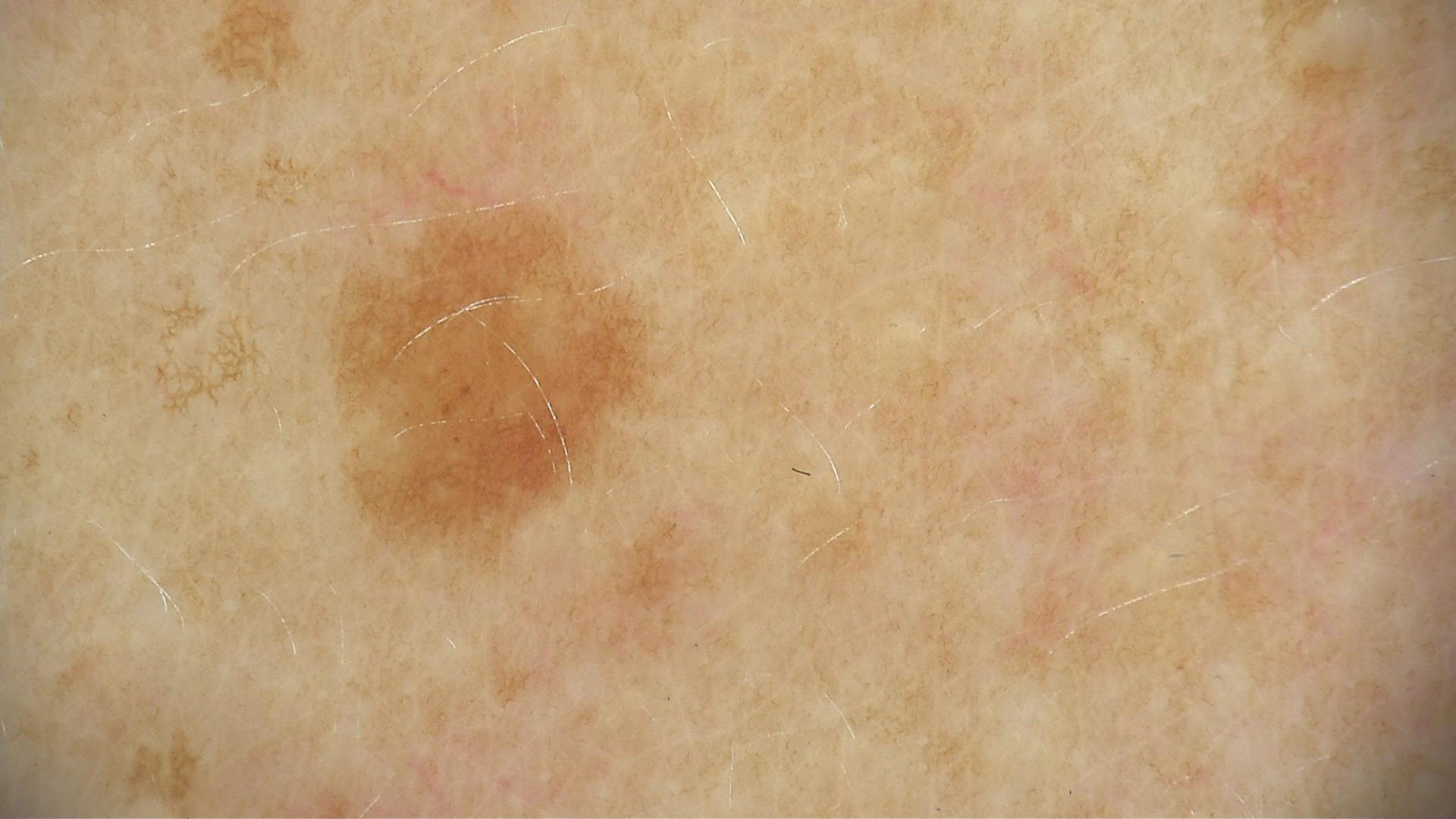Diagnosed as a benign lesion — a dysplastic junctional nevus.